This is a dermoscopic photograph of a skin lesion; a female patient aged approximately 65: 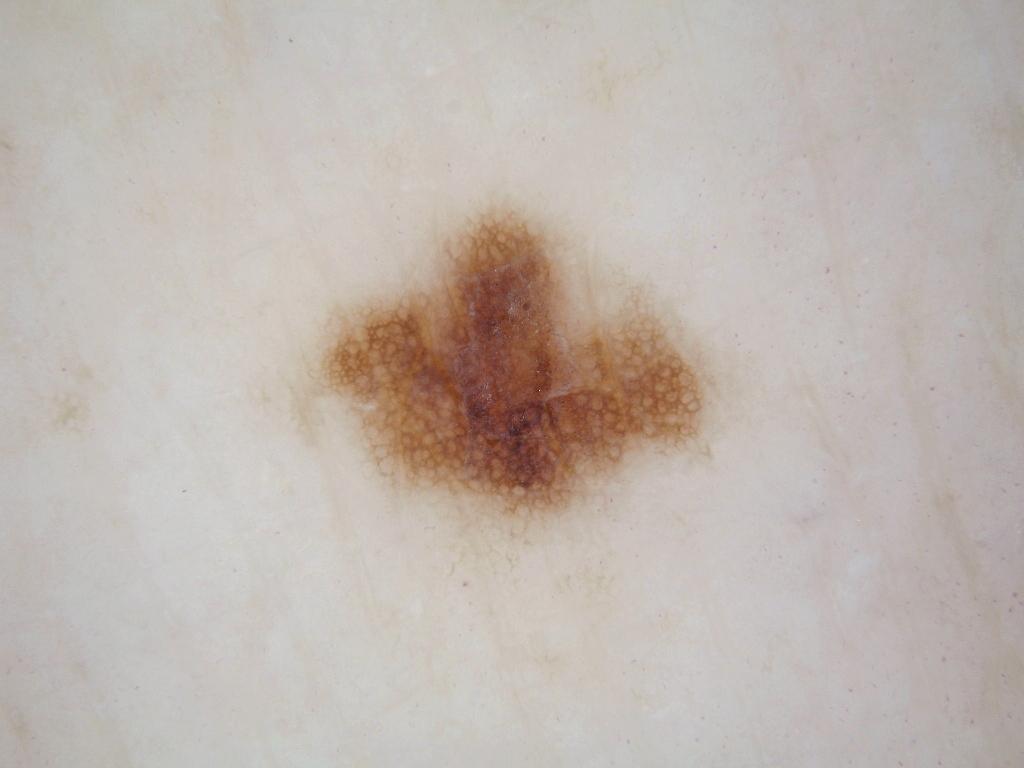Q: Where is the lesion located?
A: left=309, top=203, right=720, bottom=537
Q: What dermoscopic features are present?
A: pigment network
Q: Lesion extent?
A: ~11% of the field
Q: What did the assessment conclude?
A: a melanocytic nevus, a benign lesion